A skin lesion imaged with a dermatoscope.
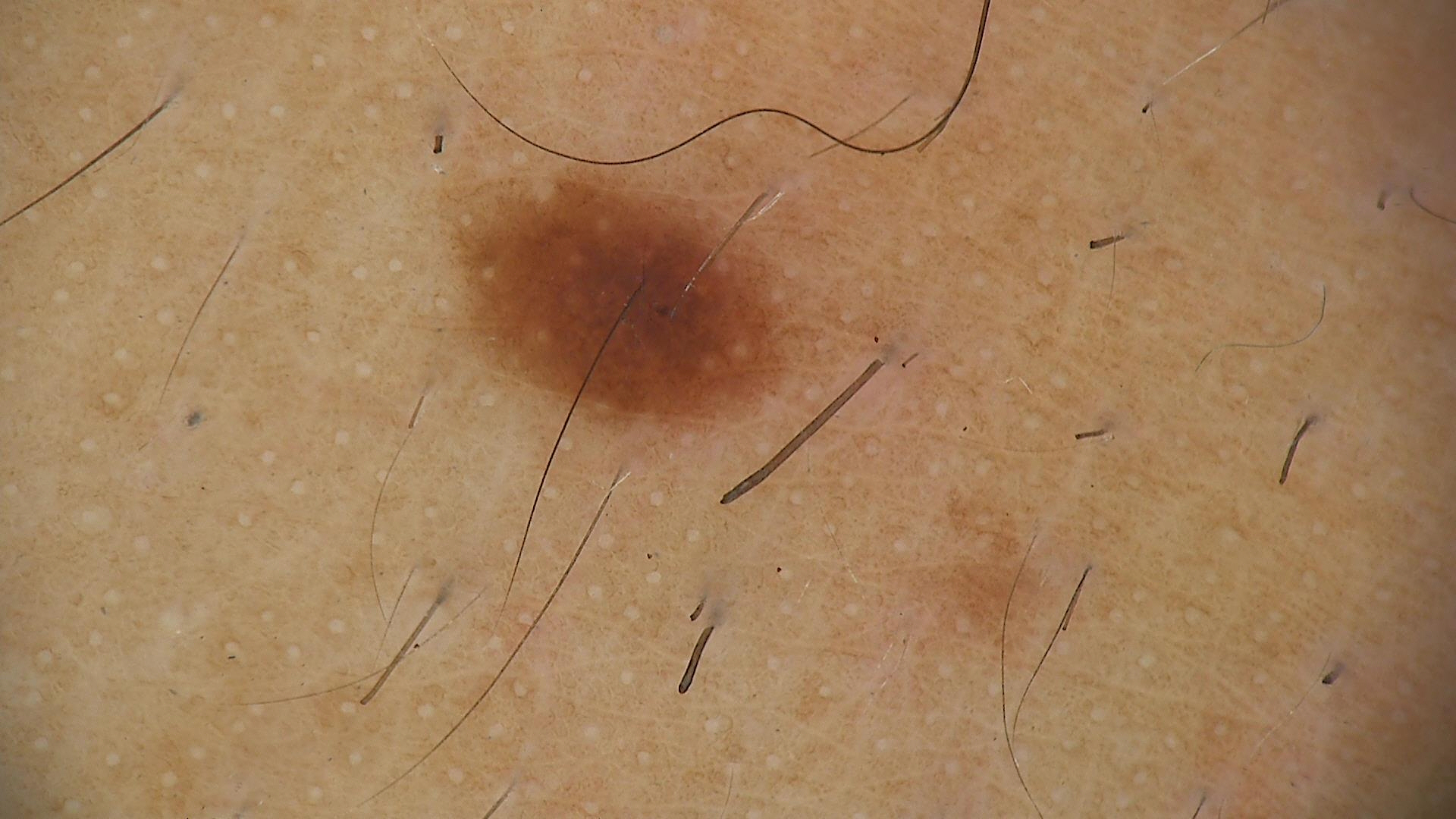  diagnosis:
    name: dysplastic junctional nevus
    code: jd
    malignancy: benign
    super_class: melanocytic
    confirmation: expert consensus